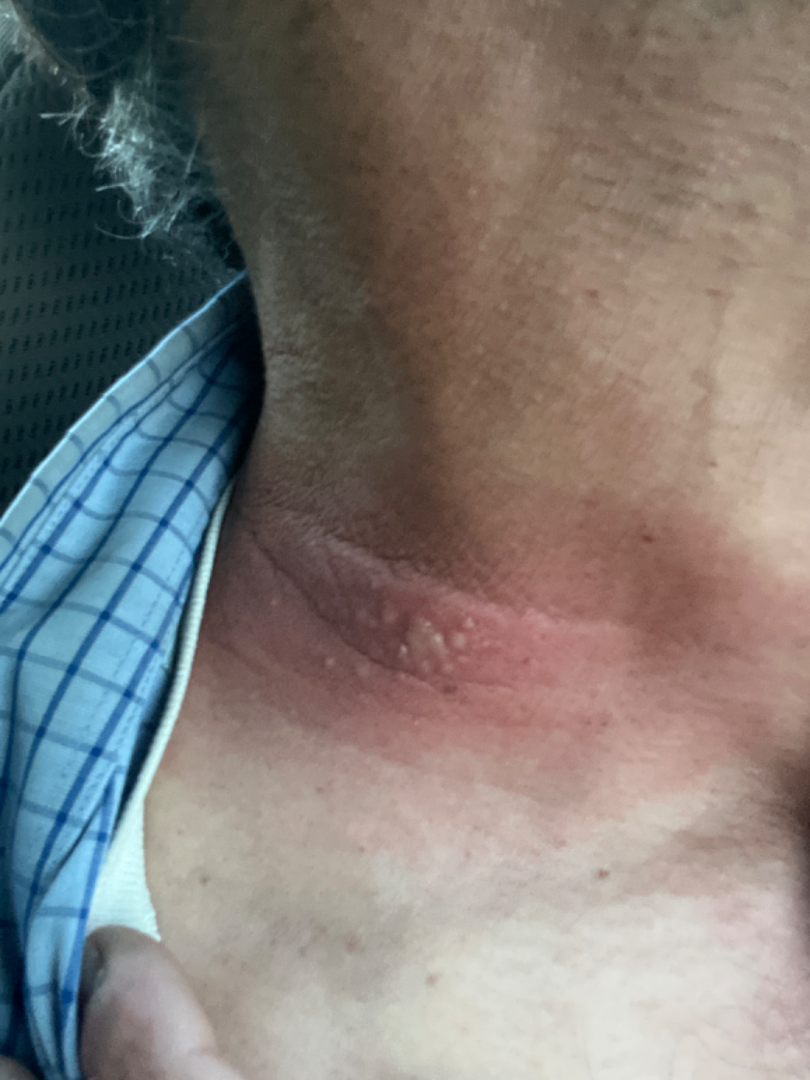<summary>
  <shot_type>at an angle</shot_type>
  <body_site>head or neck</body_site>
  <differential>
    <leading>Herpes Zoster</leading>
    <considered>Allergic Contact Dermatitis, Herpes Simplex</considered>
  </differential>
</summary>